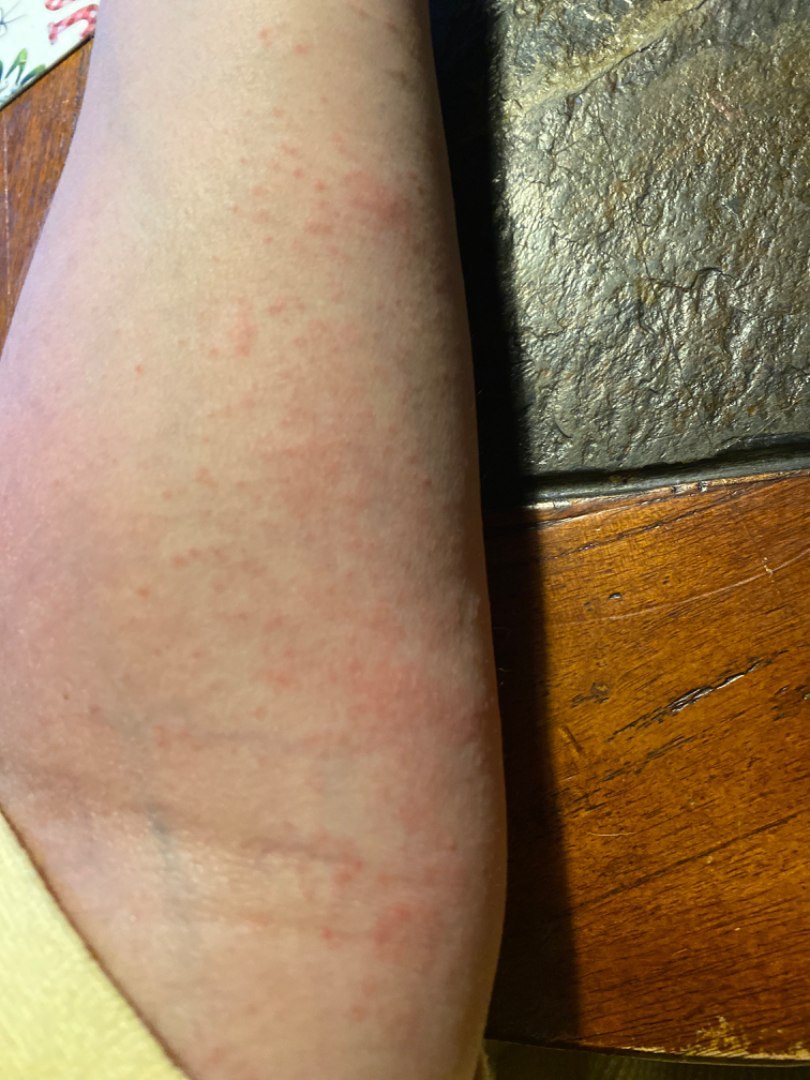Background:
The subject is a female aged 40–49. A close-up photograph. The lesion involves the arm, leg, back of the torso, front of the torso and head or neck. The patient notes the lesion is raised or bumpy. The patient also reports fatigue and fever. The patient described the issue as a rash.
Findings:
On remote dermatologist review, the primary impression is Allergic Contact Dermatitis; also consider Eczema; lower on the differential is Viral Exanthem; less probable is Hypersensitivity.